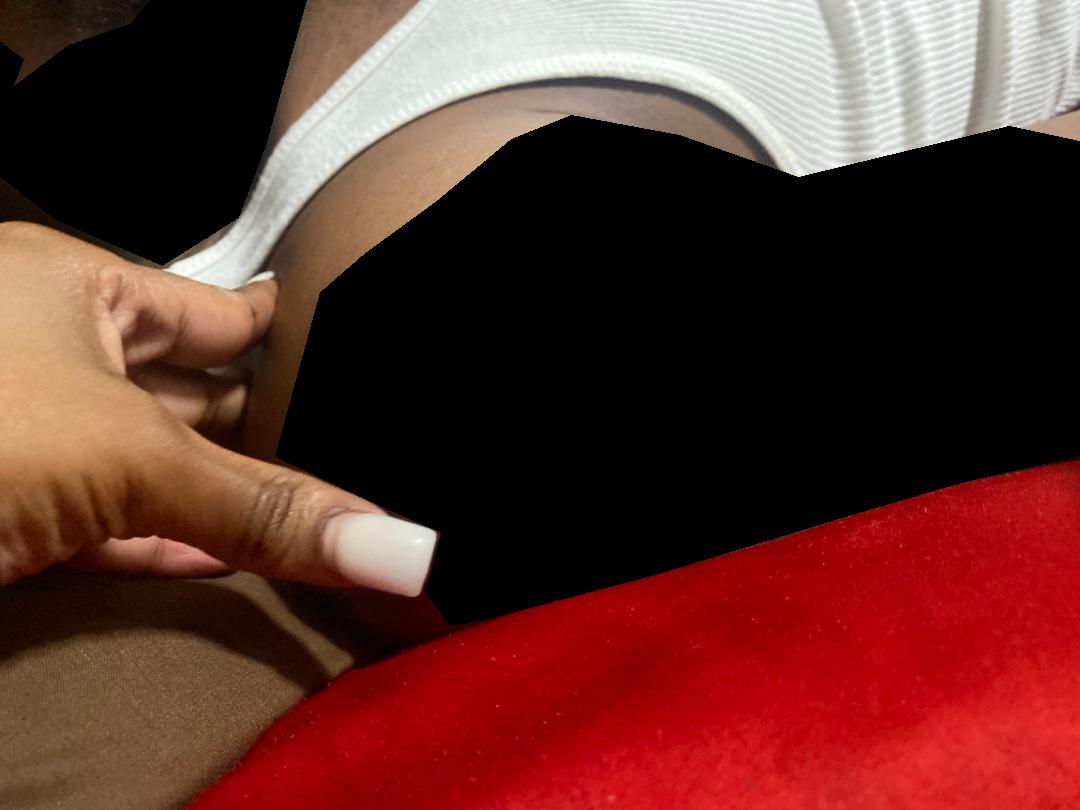Impression: The image was not sufficient for the reviewer to characterize the skin condition. History: Present for less than one week. Close-up view. Located on the arm. The lesion is described as raised or bumpy.